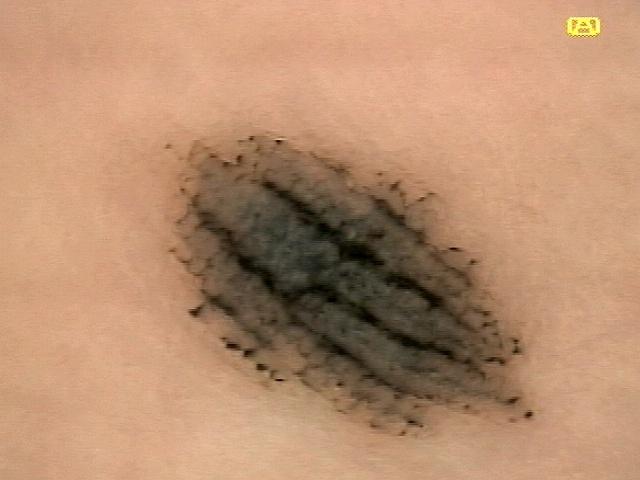Summary: A dermoscopic close-up of a skin lesion. A male subject in their 30s. The lesion is on an acral site (palms or soles). Pathology: The biopsy diagnosis was a nevus.